The patient is a male aged 28-32; a dermoscopic close-up of a skin lesion — 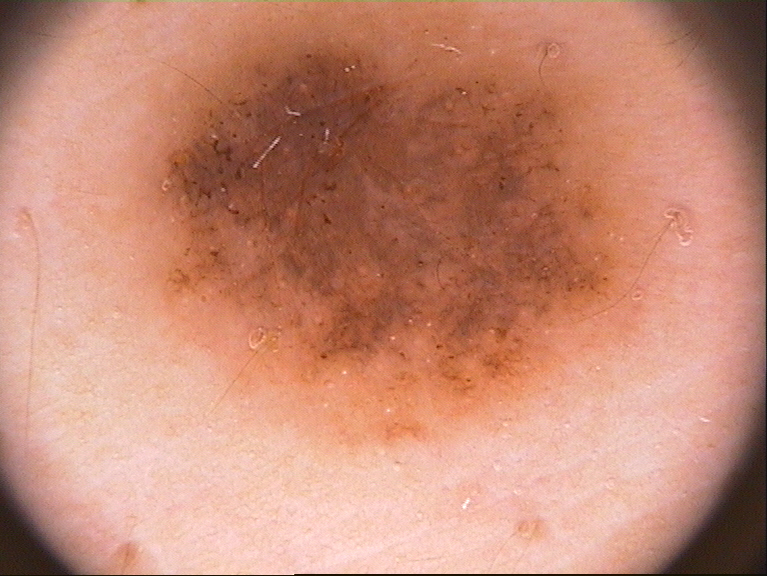Findings: Dermoscopically, the lesion shows globules. With coordinates (x1, y1, x2, y2), lesion location: [121,3,675,452]. Impression: Clinically diagnosed as a melanocytic nevus.